Dermoscopy of a skin lesion:
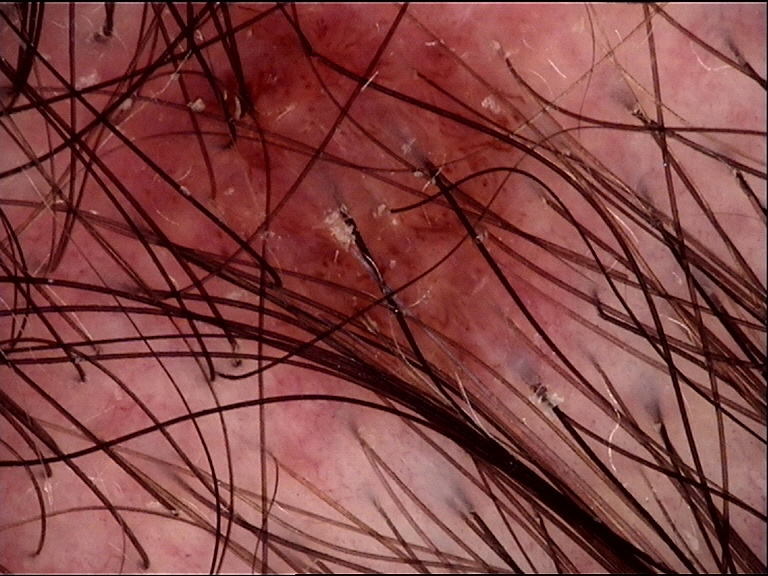| field | value |
|---|---|
| diagnostic label | dysplastic junctional nevus (expert consensus) |